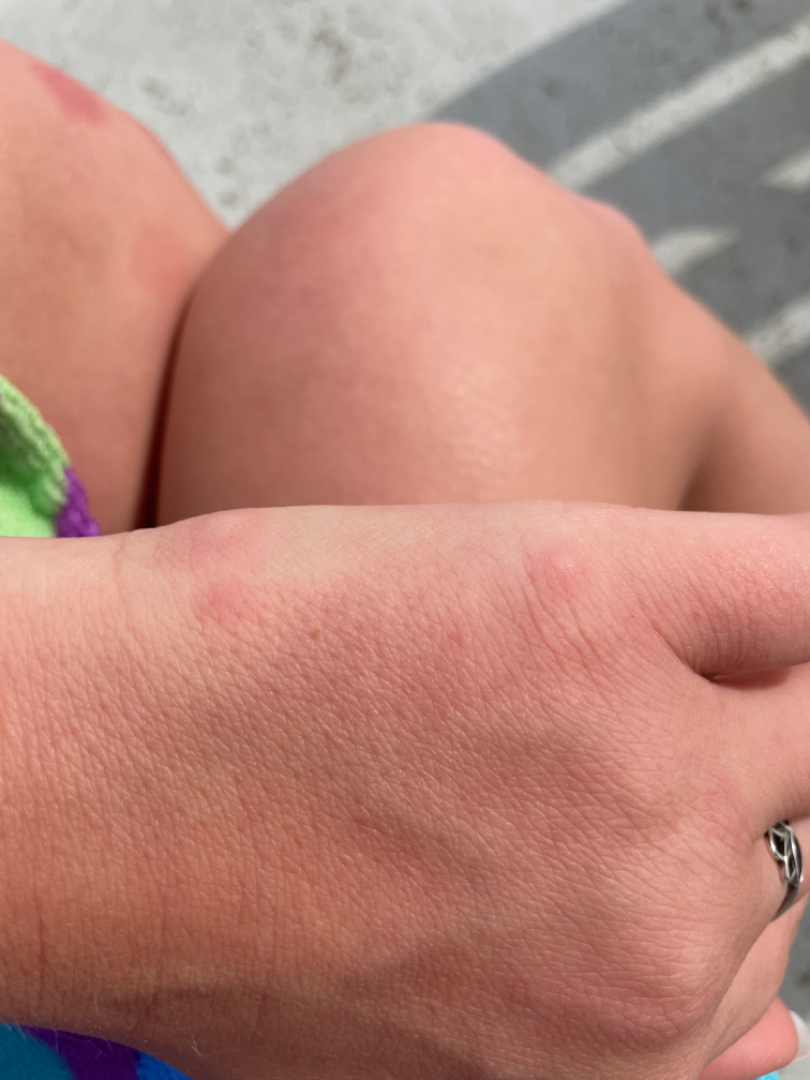The skin condition could not be confidently assessed from this image. The patient reports the lesion is raised or bumpy. The subject is 18–29, female. Self-categorized by the patient as a rash. Present for about one day. Located on the front of the torso, top or side of the foot, back of the hand, arm, leg and head or neck. Reported lesion symptoms include itching, burning and enlargement. The photo was captured at an angle.